Dermoscopy of a skin lesion.
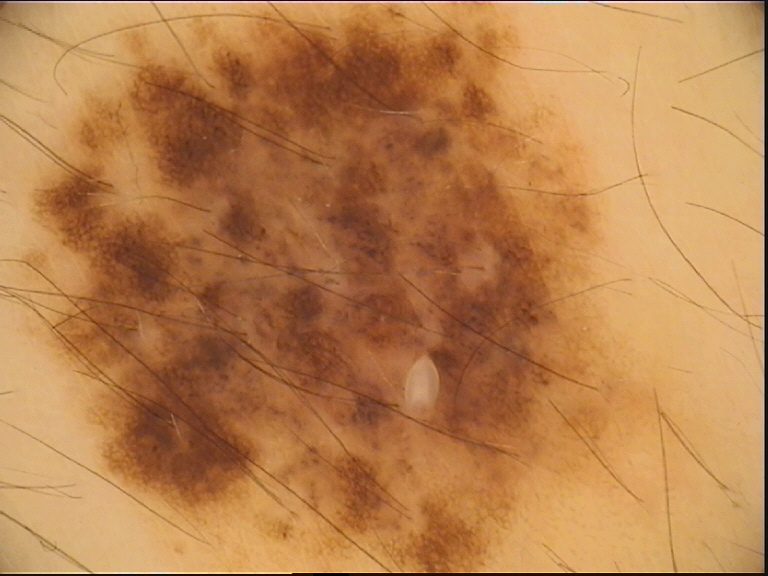Labeled as a benign lesion — a congenital dysplastic compound nevus.